The photo was captured at an angle; the contributor is male; located on the arm — 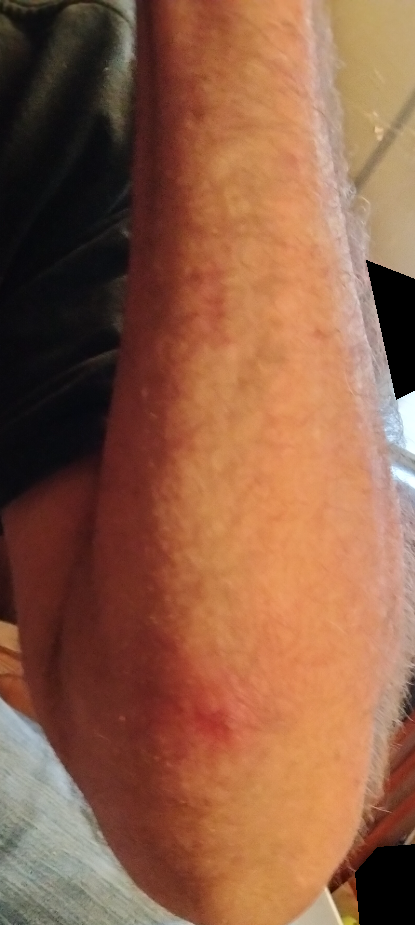Texture is reported as raised or bumpy and fluid-filled. Reported lesion symptoms include bothersome appearance. Associated systemic symptoms include fatigue. On remote dermatologist review: consistent with pustules.